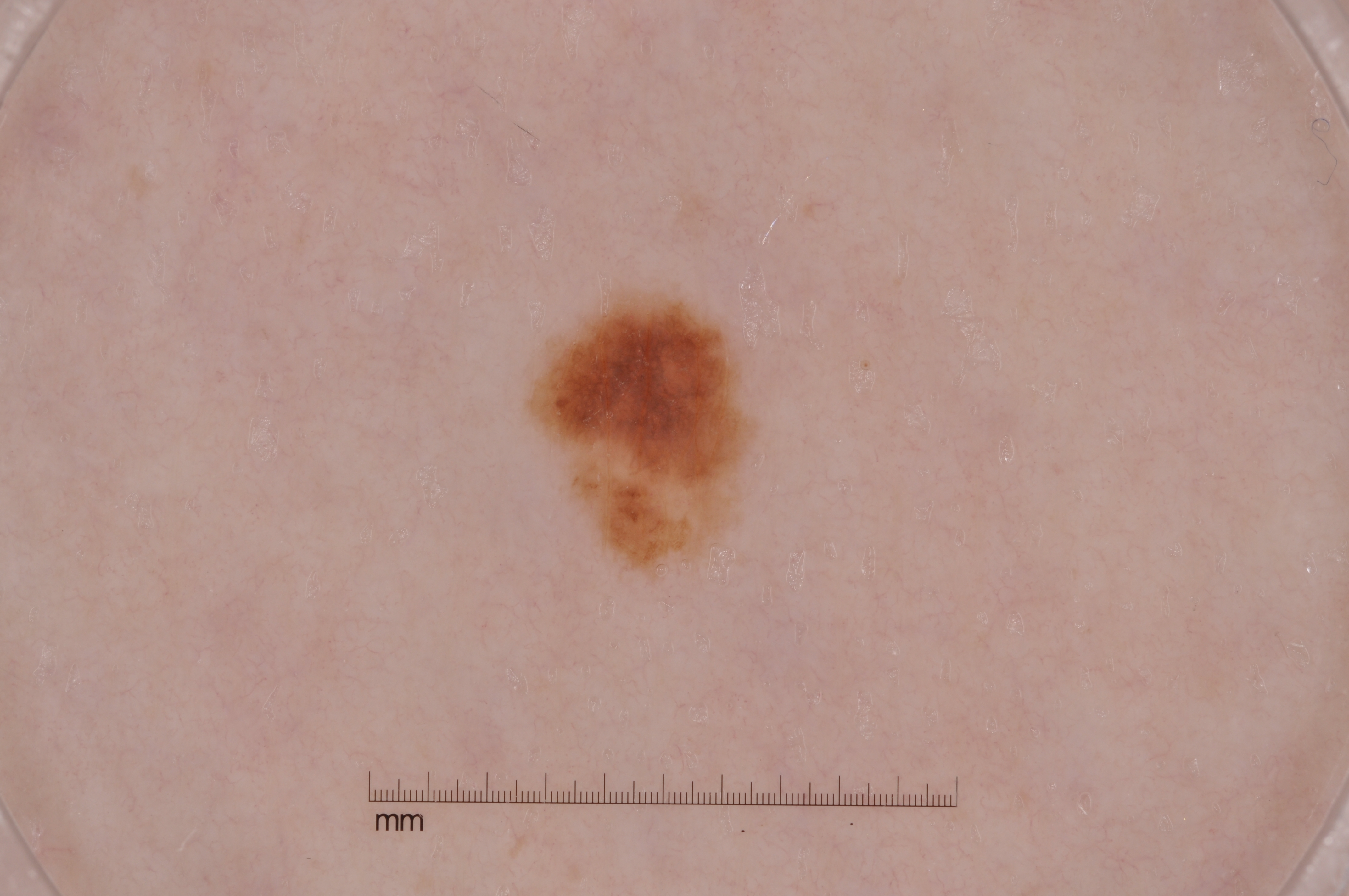  image:
    modality: dermoscopy
  lesion_location:
    bbox_xyxy:
      - 538
      - 294
      - 748
      - 567
  diagnosis:
    name: melanocytic nevus
    malignancy: benign
    lineage: melanocytic
    provenance: clinical